A dermoscopic image of a skin lesion.
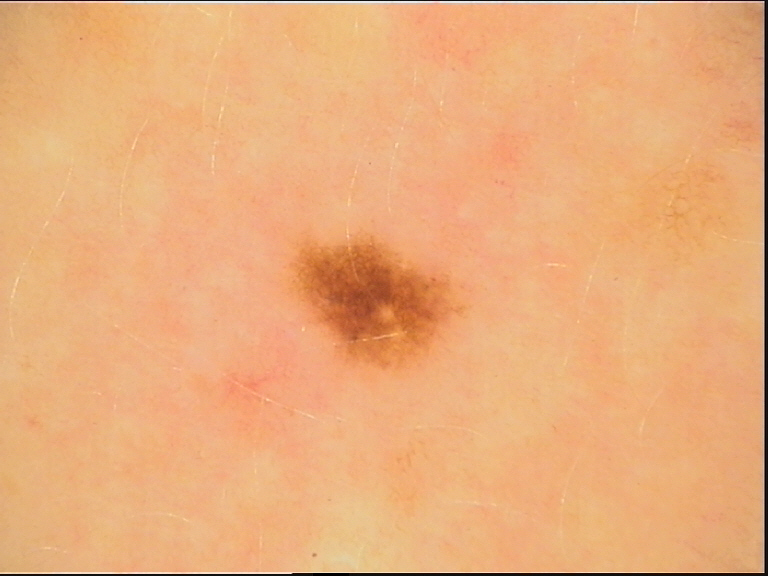Q: What is this lesion?
A: dysplastic junctional nevus (expert consensus)